Close-up view.
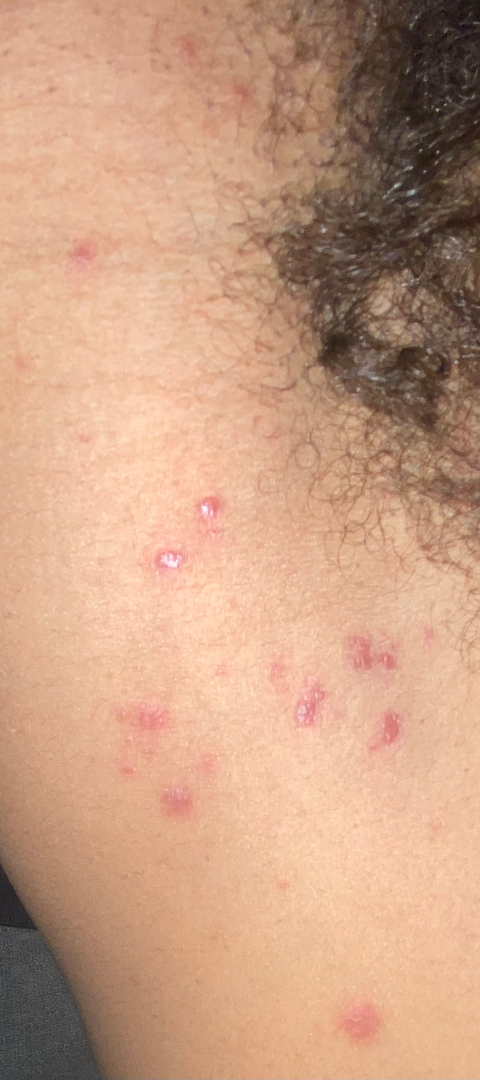Reviewed remotely by one dermatologist: favoring Lichen planus/lichenoid eruption; possibly Drug Rash; less probable is Verruca vulgaris.